The patient is Fitzpatrick II; a female patient aged 58 to 62; a contact-polarized dermoscopy image of a skin lesion:
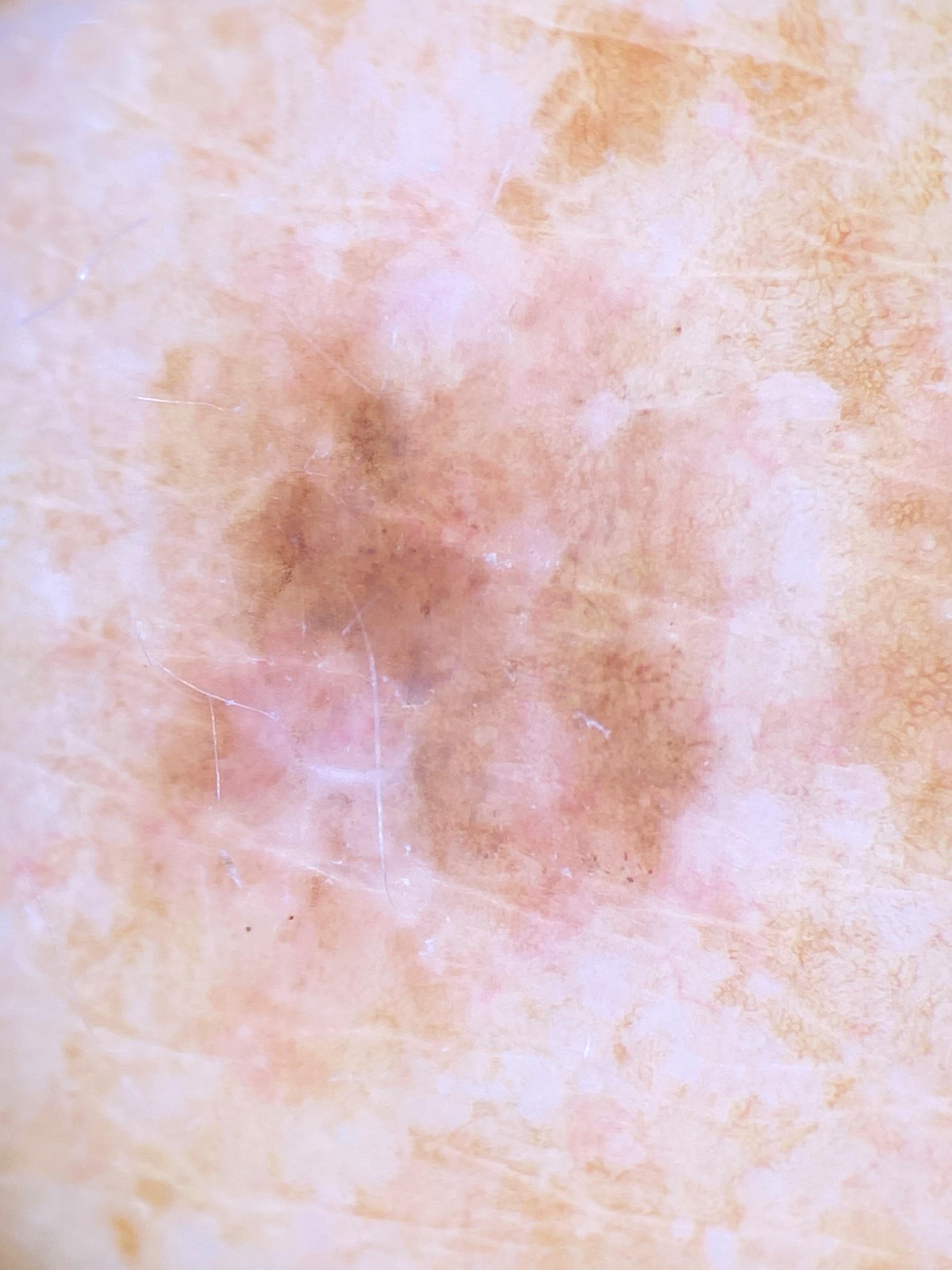  lesion_location:
    region: the trunk
    detail: the posterior trunk
  diagnosis:
    name: Nevus
    malignancy: benign
    confirmation: histopathology
    lineage: melanocytic